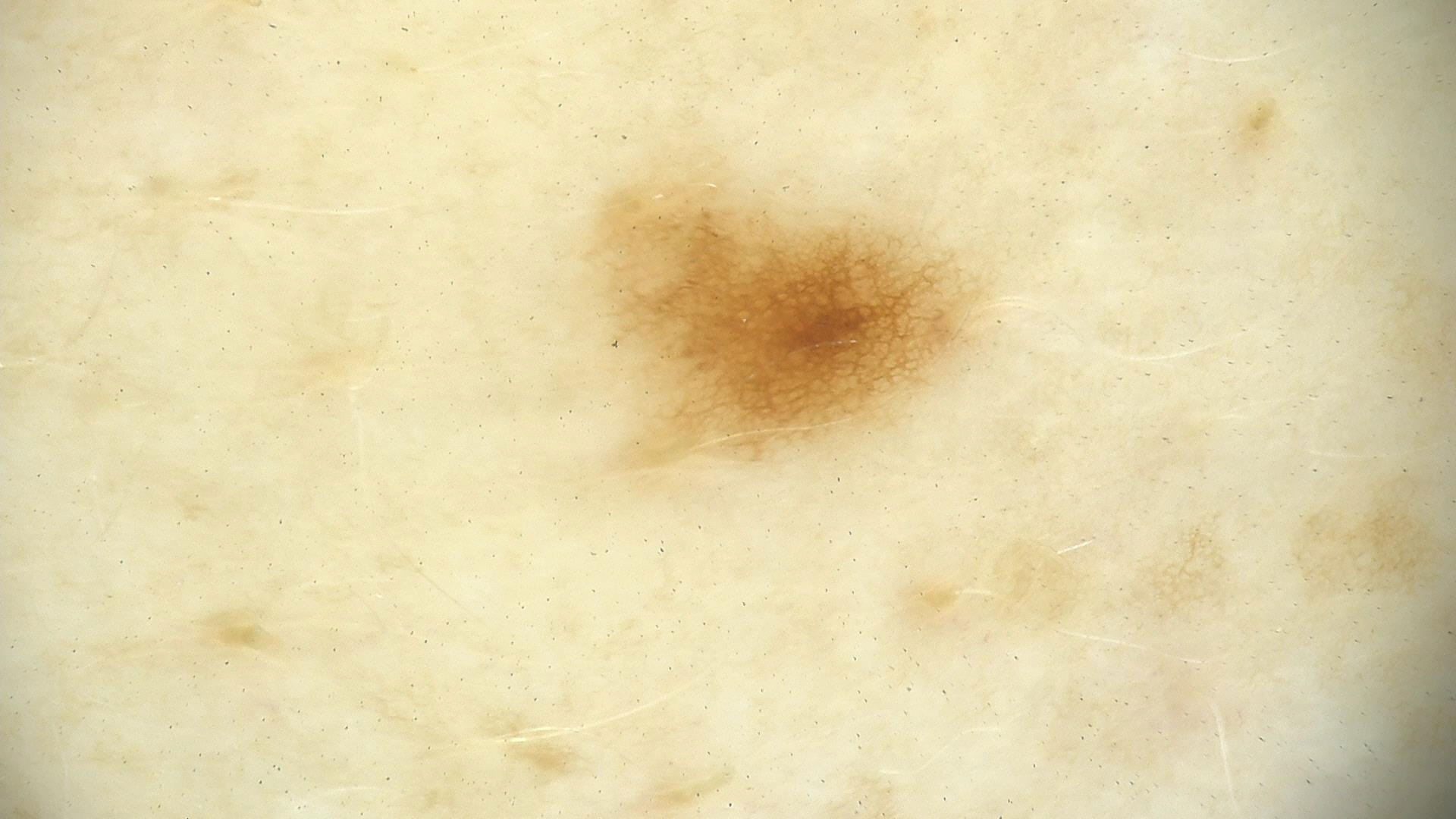imaging=dermoscopy
assessment=junctional nevus (expert consensus)